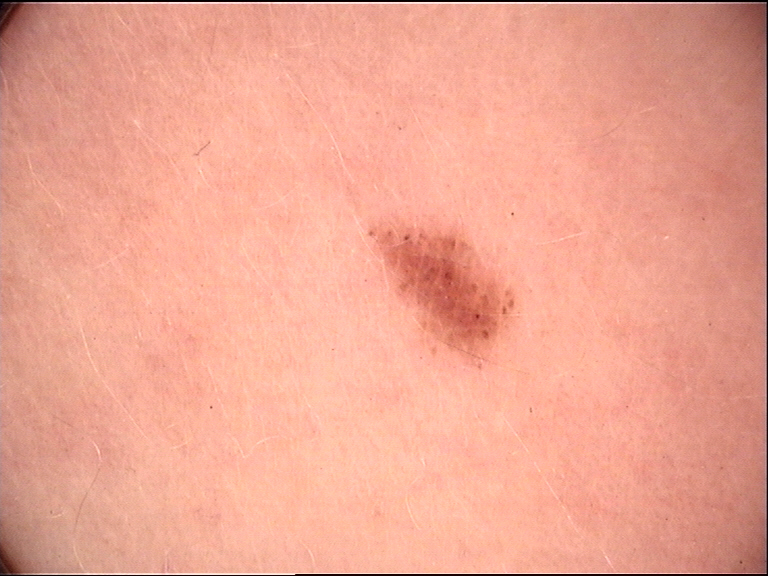Diagnosed as an acral dysplastic junctional nevus.